The patient was assessed as Fitzpatrick skin type I. History notes prior malignancy (patient or family). A clinical close-up photograph of a skin lesion: 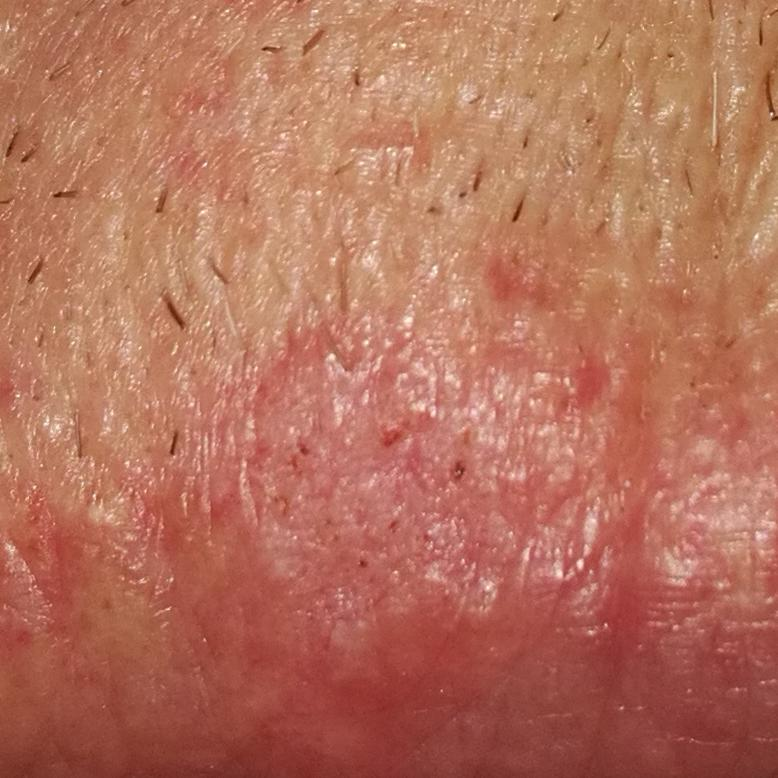Located on a lip.
The lesion measures approximately 8 × 8 mm.
Per patient report, the lesion itches.
The clinical impression was a lesion with uncertain malignant potential — an actinic keratosis.